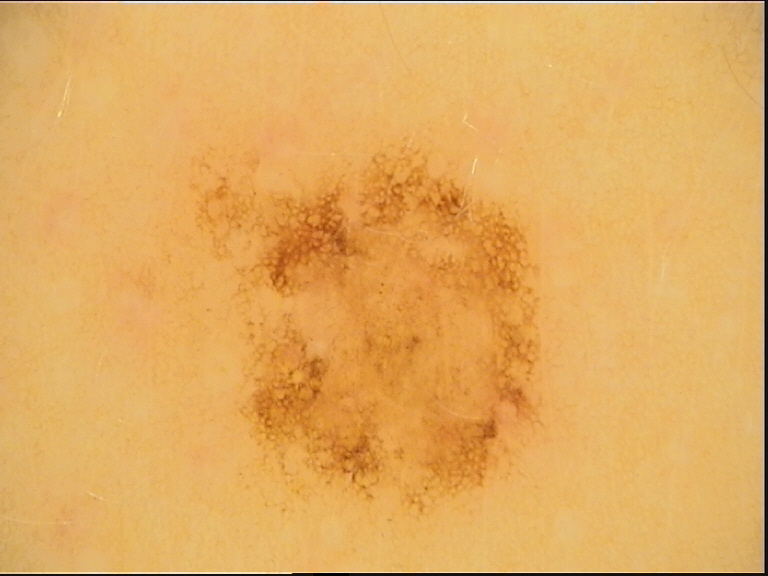A dermoscopic close-up of a skin lesion. The diagnosis was a benign lesion — a dysplastic junctional nevus.